A skin lesion imaged with a dermatoscope:
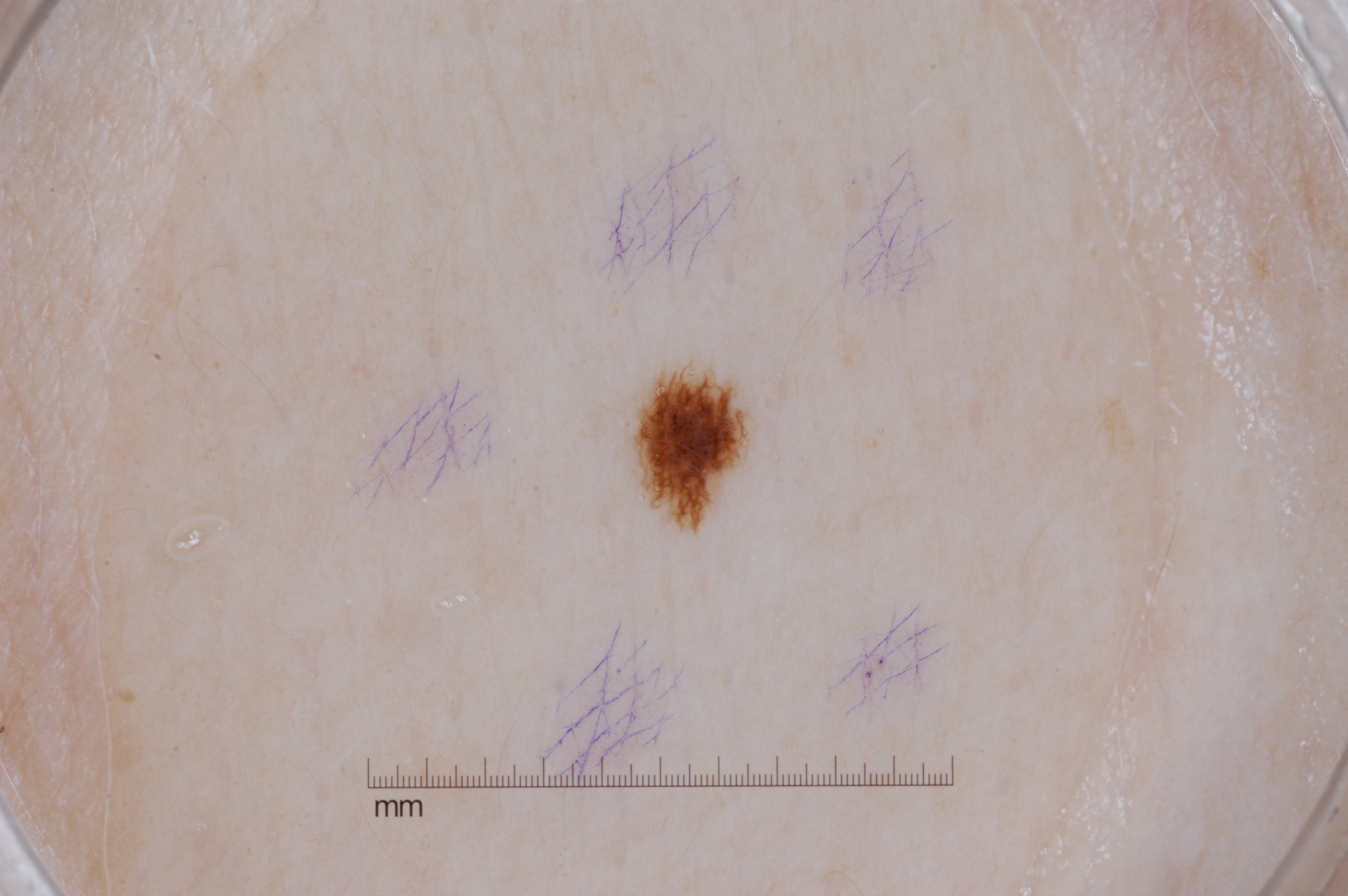Findings:
Dermoscopically, the lesion shows pigment network, with no negative network, milia-like cysts, or streaks. The lesion is bounded by 631, 361, 751, 534.
Conclusion:
Clinically diagnosed as a melanocytic nevus, a benign lesion.